A subject age 47; a clinical photograph showing a skin lesion: 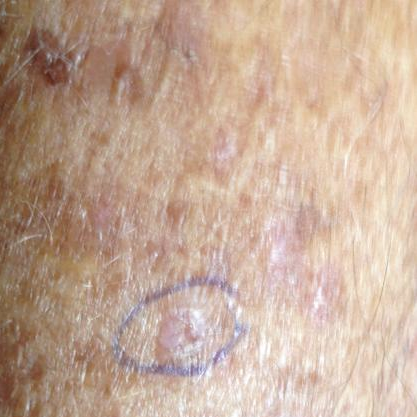region: a forearm | symptoms: itching / no elevation, no change in appearance | impression: actinic keratosis (clinical consensus).